Dermoscopy of a skin lesion: 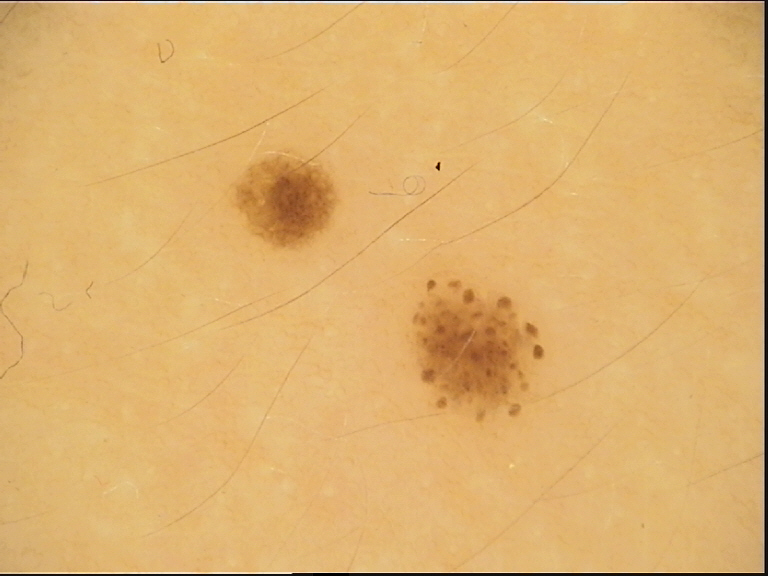Conclusion: Consistent with a dysplastic junctional nevus.